A skin lesion imaged with a dermatoscope.
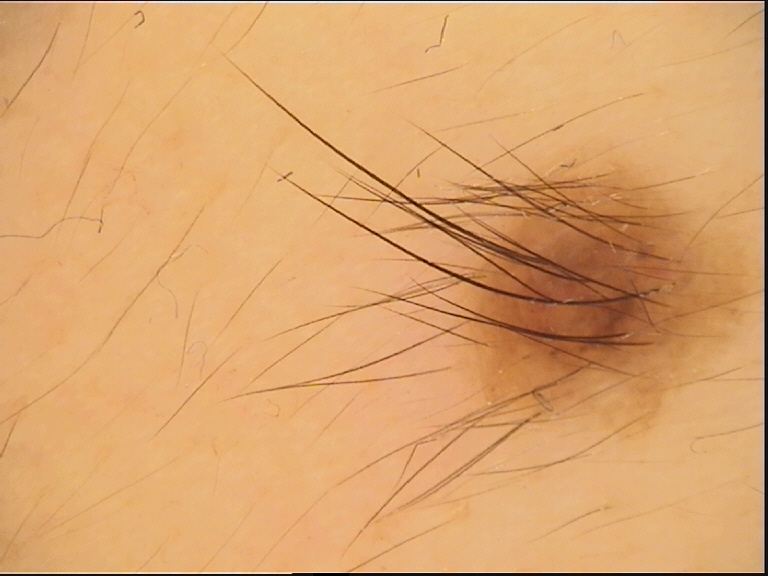Consistent with a compound lesion — a Miescher nevus.